The photograph is a close-up of the affected area: 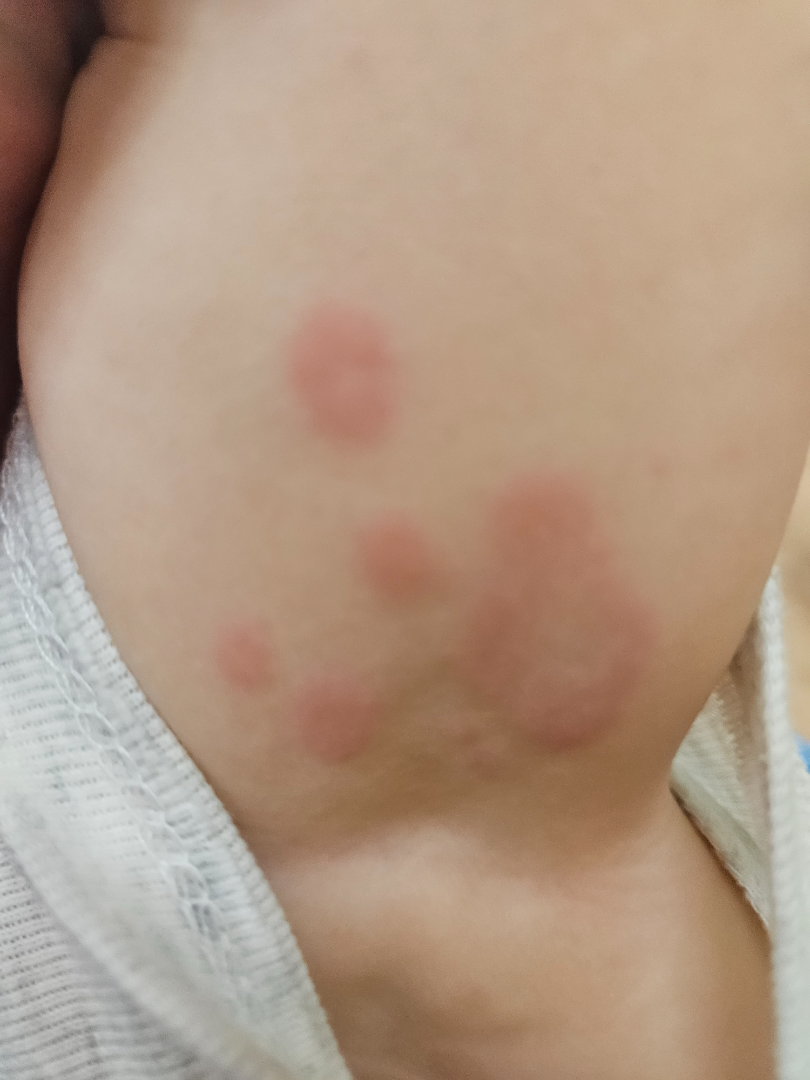Case summary:
- dermatologist impression · Drug Rash (considered); Leukocytoclastic Vasculitis (considered); Granuloma annulare (considered)